Collected as part of a research study, without a referral diagnosis · a male subject 77 years old · a skin lesion imaged with a dermatoscope — 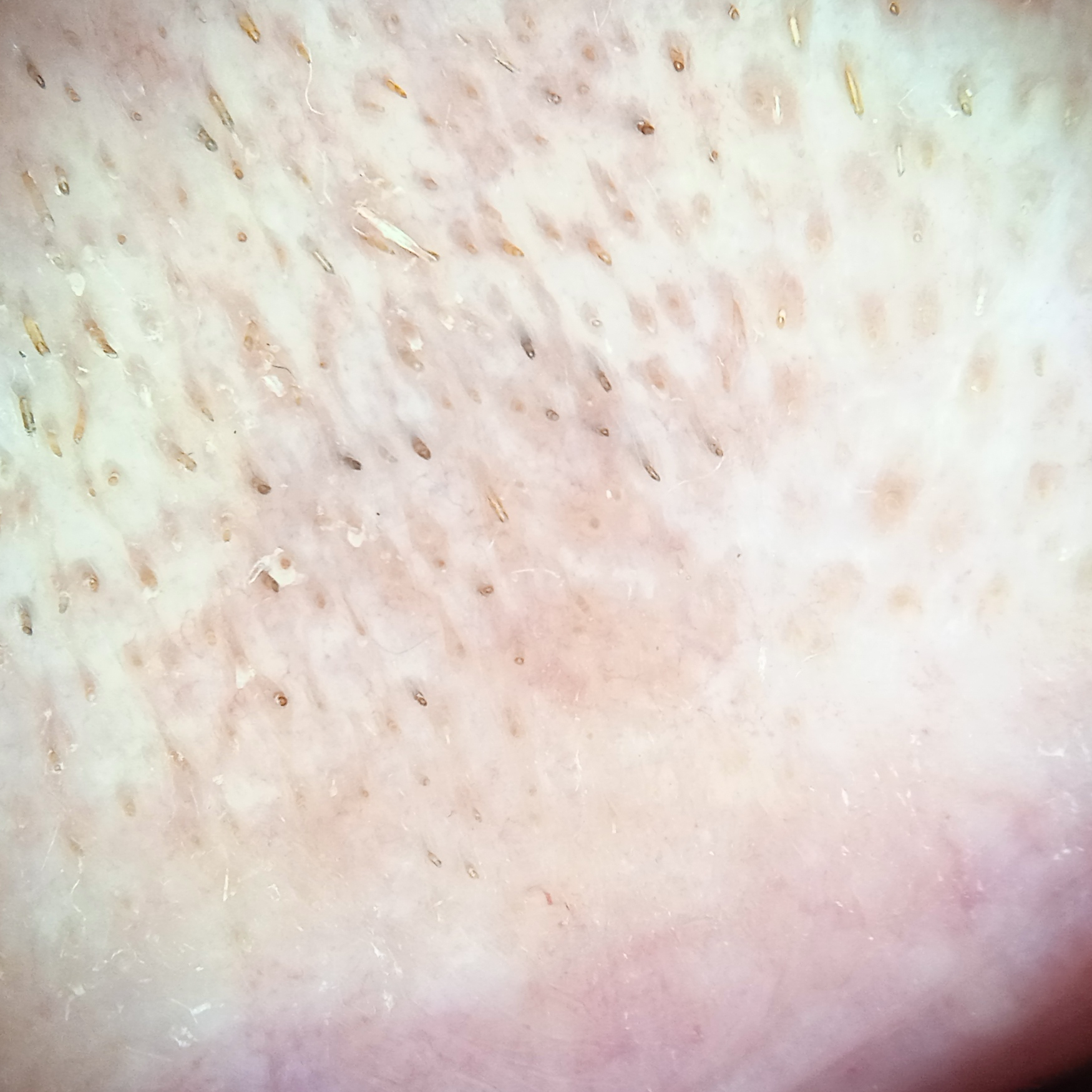The lesion involves the face. Dermatologist review favored an actinic keratosis.